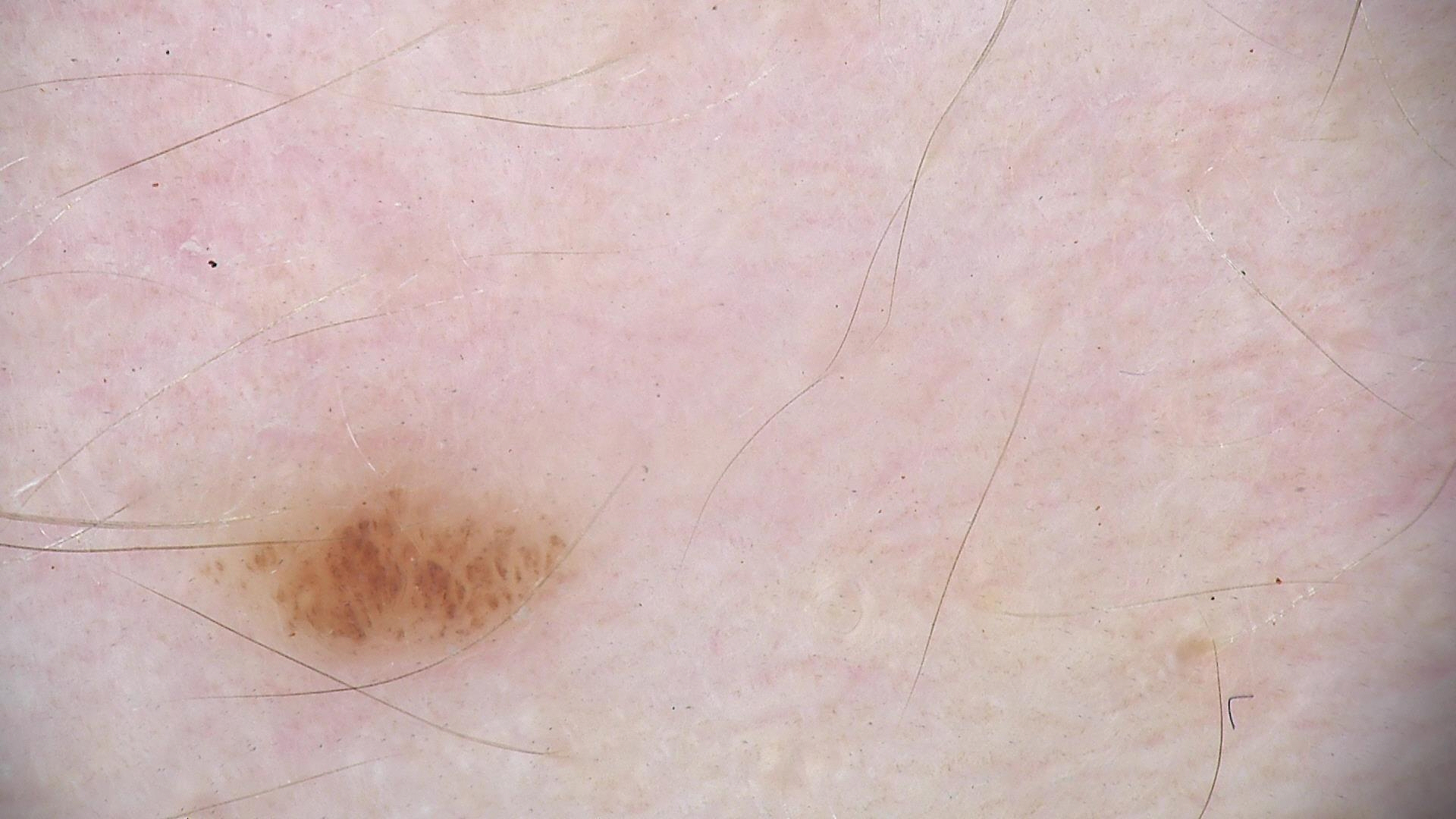Q: What kind of image is this?
A: dermatoscopy
Q: What is this lesion?
A: dysplastic junctional nevus (expert consensus)